The subject is a female aged 18–29; the photograph was taken at an angle; the affected area is the arm.
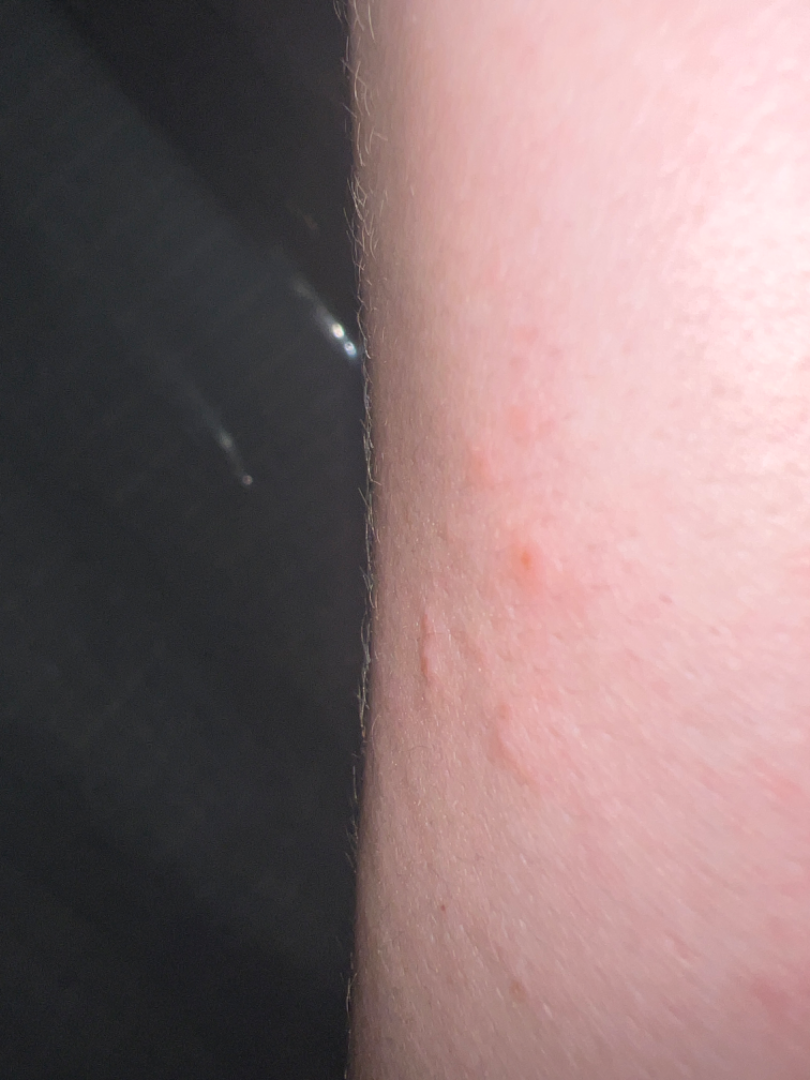Q: What is the differential diagnosis?
A: Allergic Contact Dermatitis (leading)